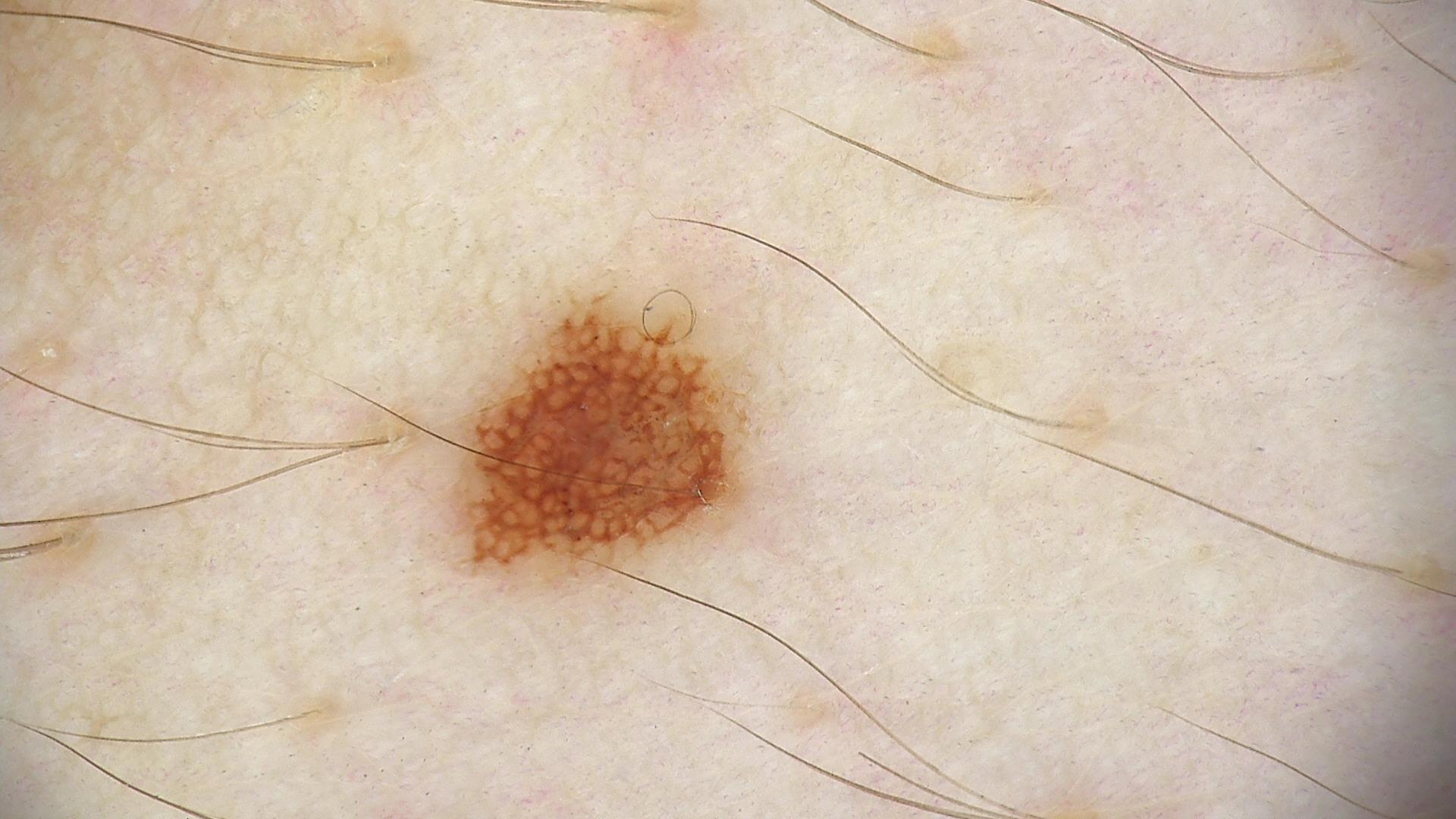{
  "image": "dermoscopy",
  "diagnosis": {
    "name": "dysplastic junctional nevus",
    "code": "jd",
    "malignancy": "benign",
    "super_class": "melanocytic",
    "confirmation": "expert consensus"
  }
}